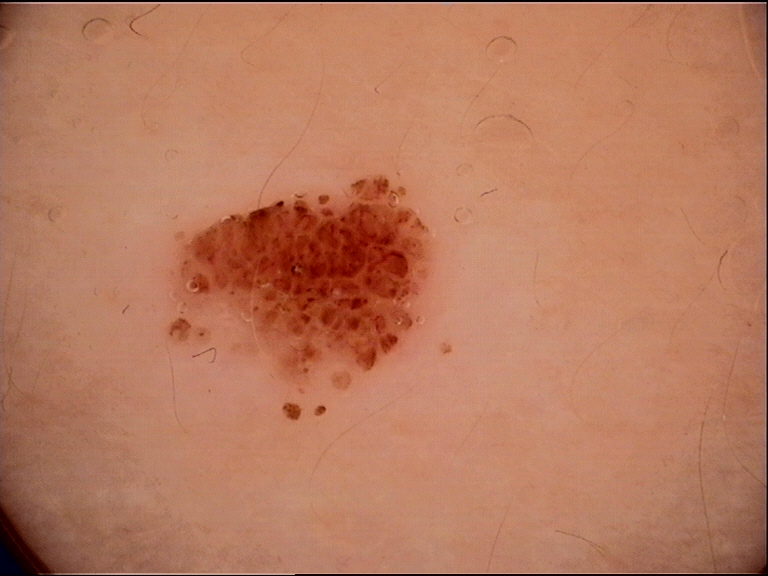Summary:
A skin lesion imaged with a dermatoscope. The morphology is that of a banal lesion.
Impression:
Labeled as a compound nevus.